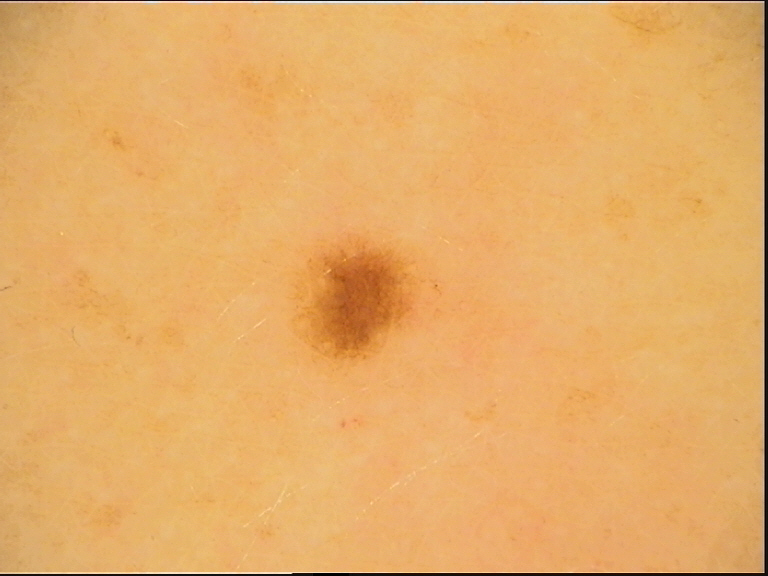The diagnostic label was a junctional nevus.